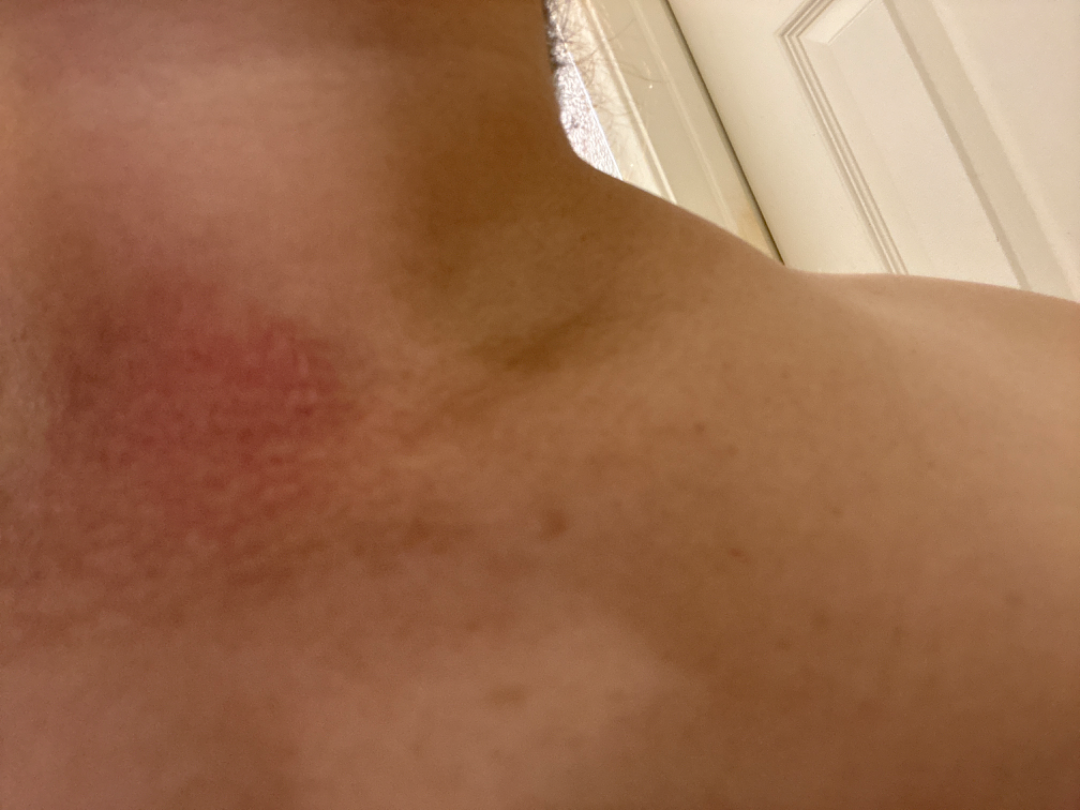Background: The lesion involves the head or neck. An image taken at an angle. Findings: The reviewing dermatologist's impression was: favoring ecchymoses; also on the differential is Eczema.